This is a dermoscopic photograph of a skin lesion. A male subject, aged approximately 45:
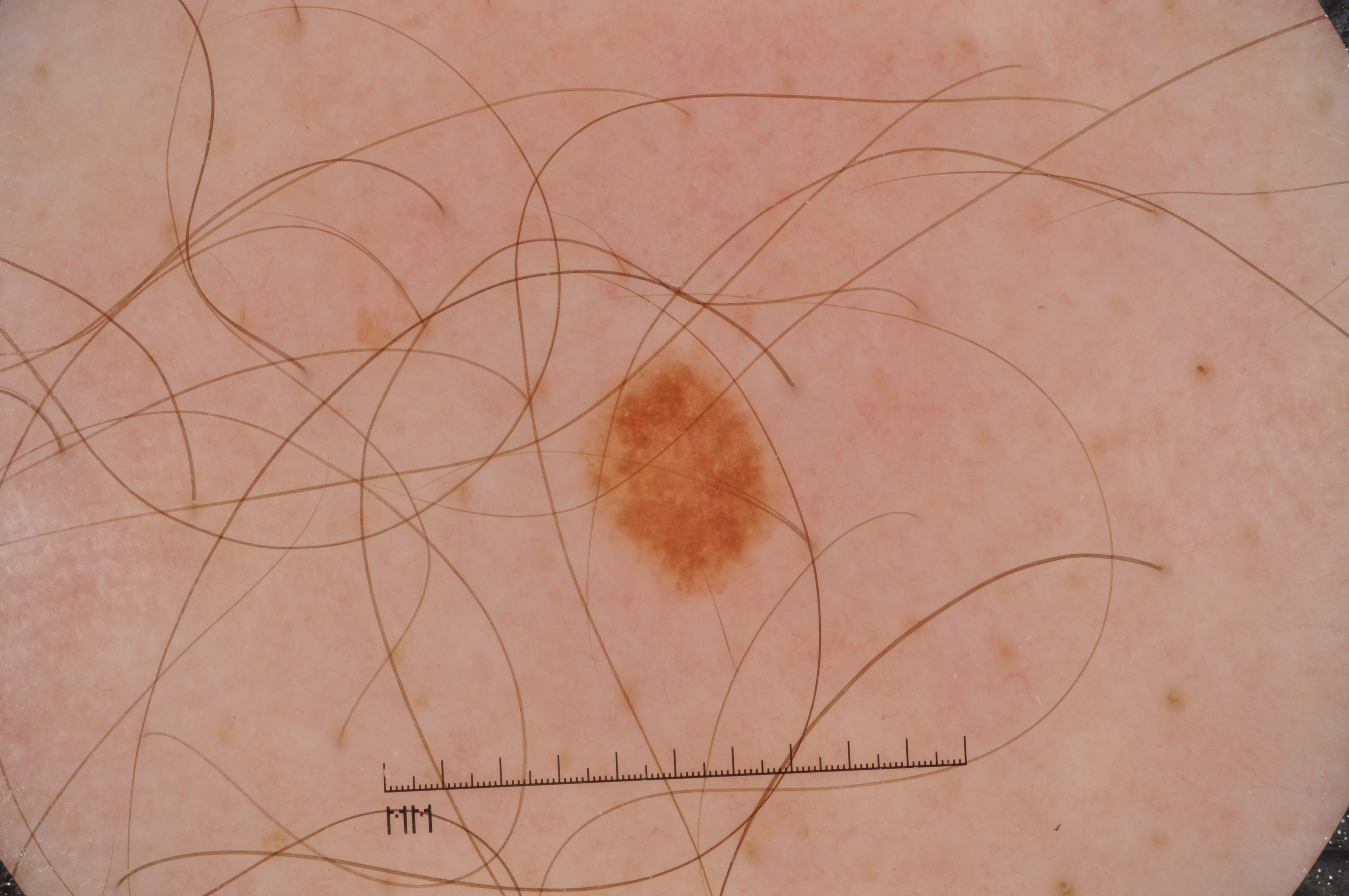Dermoscopy demonstrates negative network and milia-like cysts; no pigment network or streaks. As (left, top, right, bottom), lesion location: bbox=[561, 346, 788, 604]. A small lesion within a wider field of skin. Expert review diagnosed this as a melanocytic nevus, a benign skin lesion.